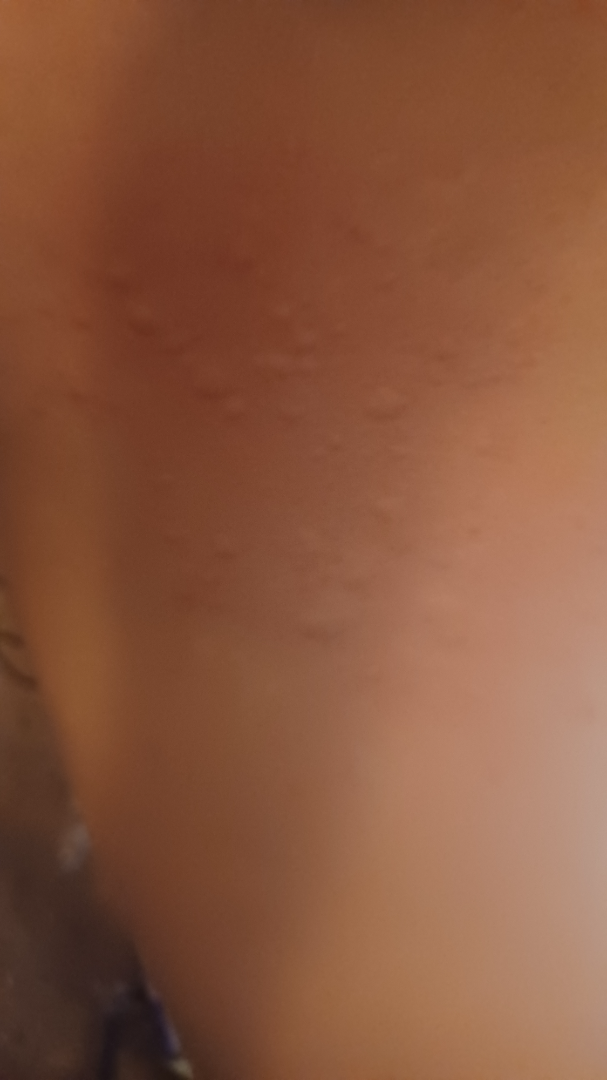The case was difficult to assess from the available photograph.